The photograph was taken at a distance · female contributor, age 18–29 · the affected area is the leg — 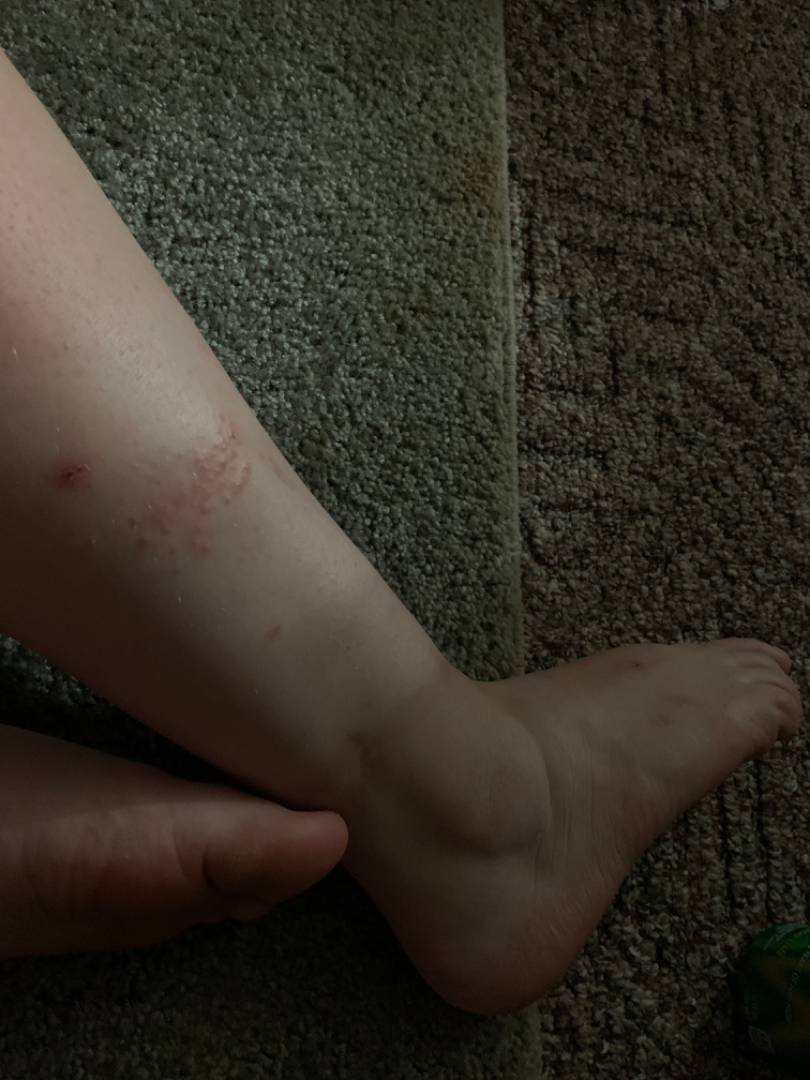{"assessment": "not assessable"}